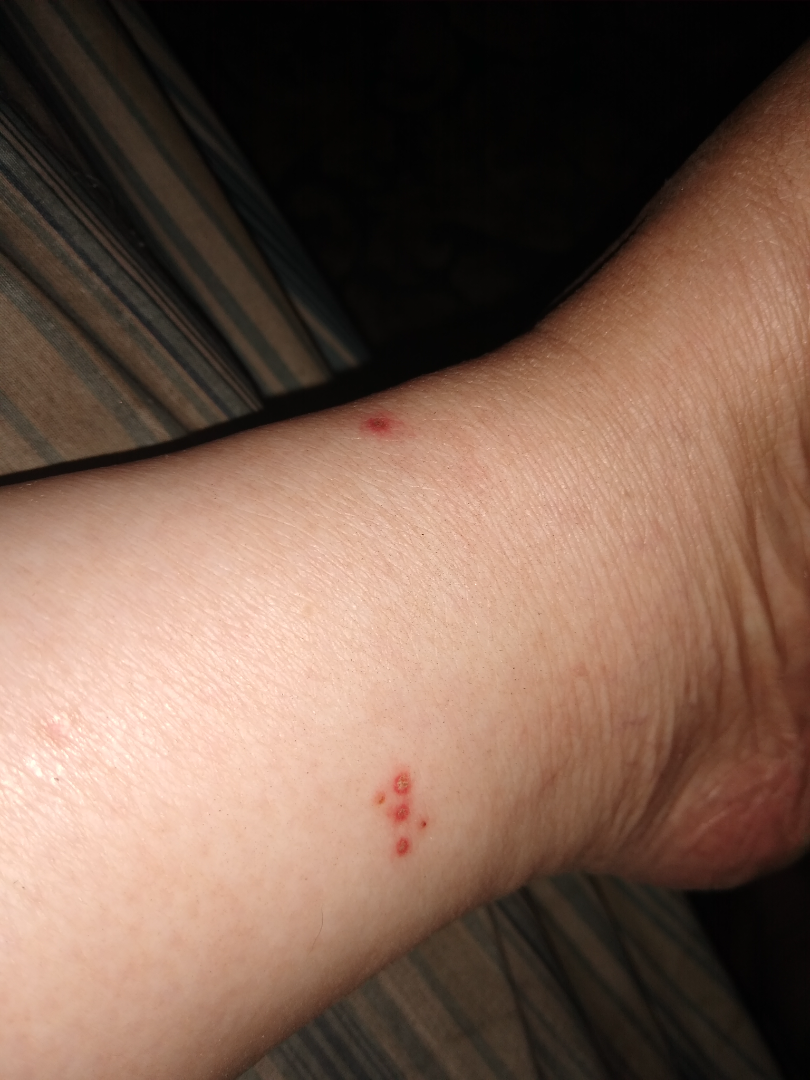Review:
On remote review of the image, the leading consideration is Insect Bite; an alternative is Impetigo; less likely is Folliculitis; less probable is Viral infection of skin; lower on the differential is Allergic Contact Dermatitis.